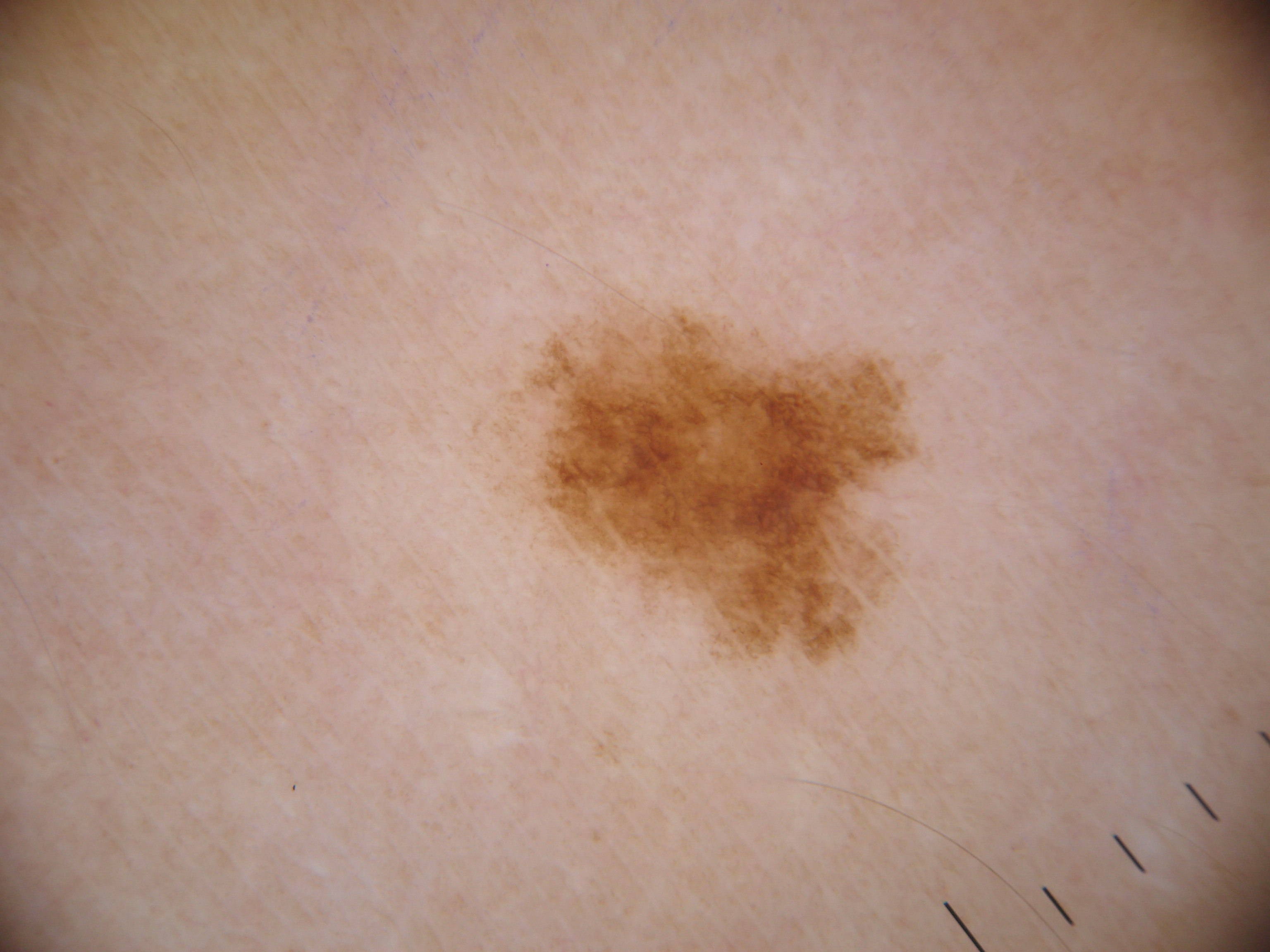A skin lesion imaged with a dermatoscope. On dermoscopy, the lesion shows pigment network. In (x1, y1, x2, y2) order, the lesion's extent is [437,271,962,688]. Biopsy-confirmed as a melanoma.